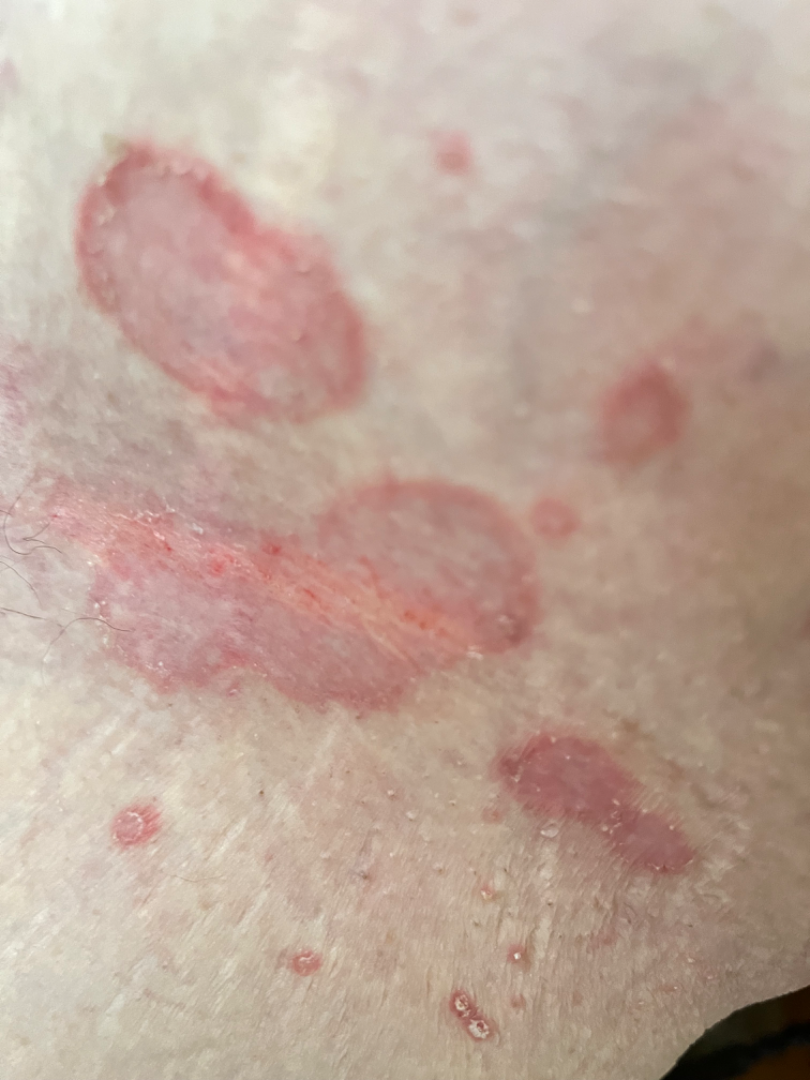Close-up view. Texture is reported as flat. The front of the torso is involved. Symptoms reported: enlargement. Fitzpatrick phototype III. Male contributor, age 70–79. The patient notes the condition has been present for one to four weeks. The patient described the issue as a rash. One reviewing dermatologist: the leading consideration is Inverse psoriasis; also raised was Candida; the differential also includes Seborrheic Dermatitis.